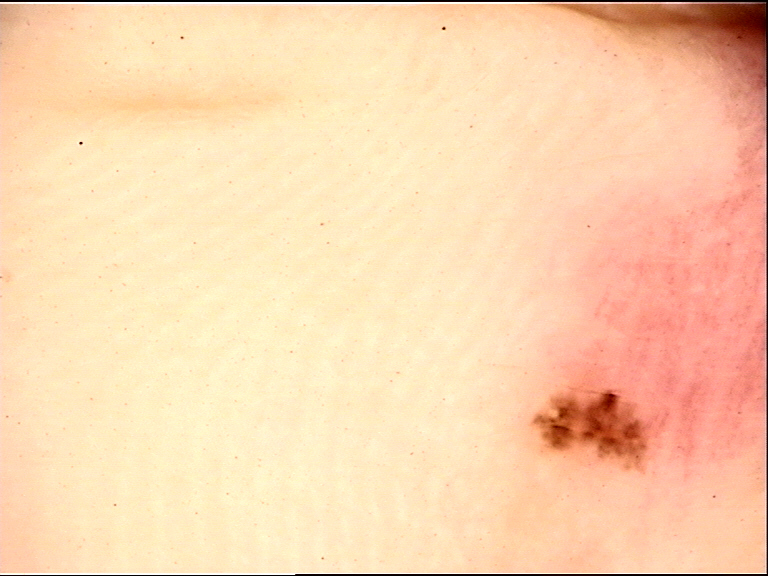Case:
– diagnosis: acral dysplastic junctional nevus (expert consensus)